Dermoscopy of a skin lesion. The patient is a male in their mid-20s — 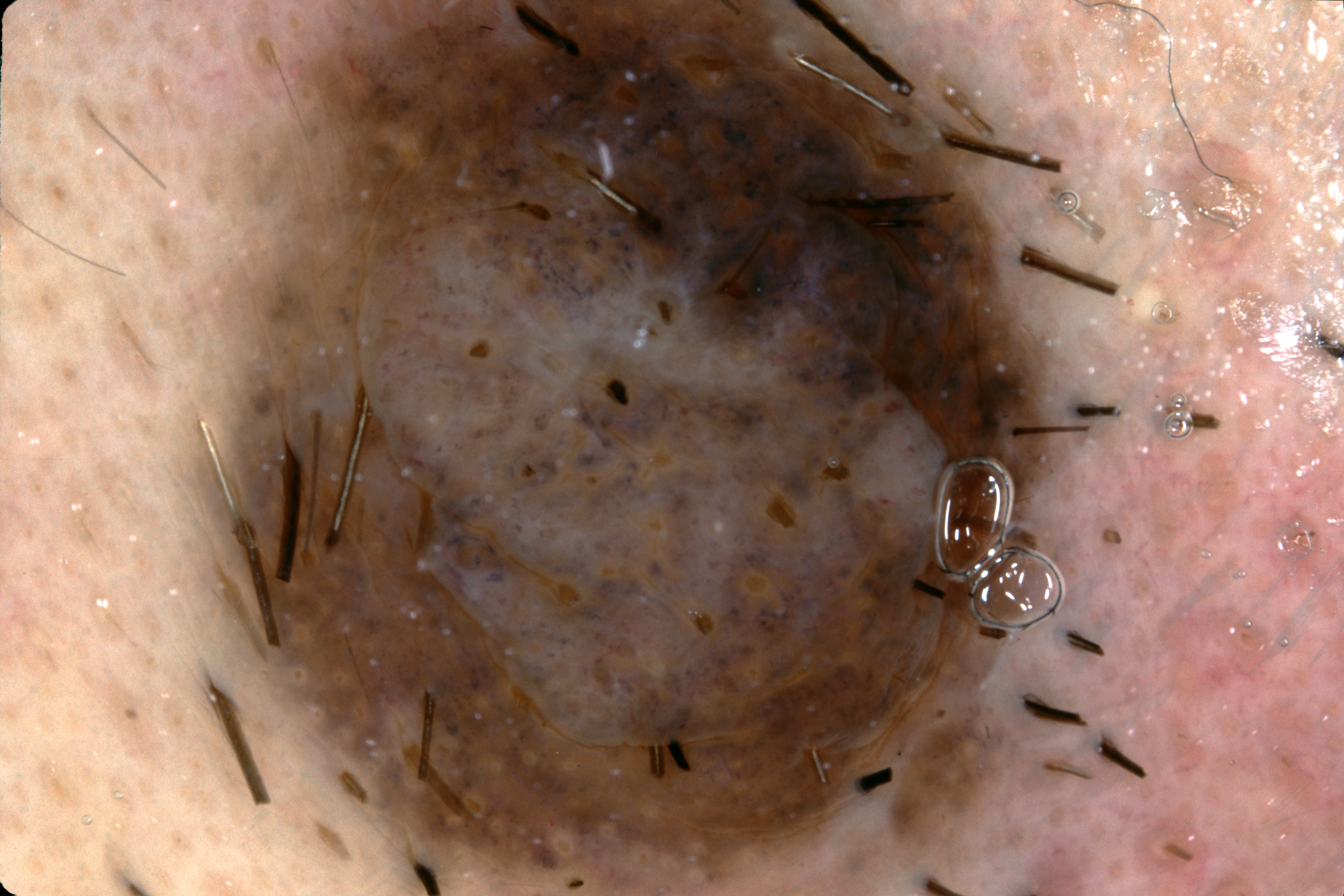lesion location — <box>195, 2, 1082, 894</box> | absent dermoscopic findings — negative network, pigment network, streaks, and milia-like cysts | diagnostic label — a melanocytic nevus.